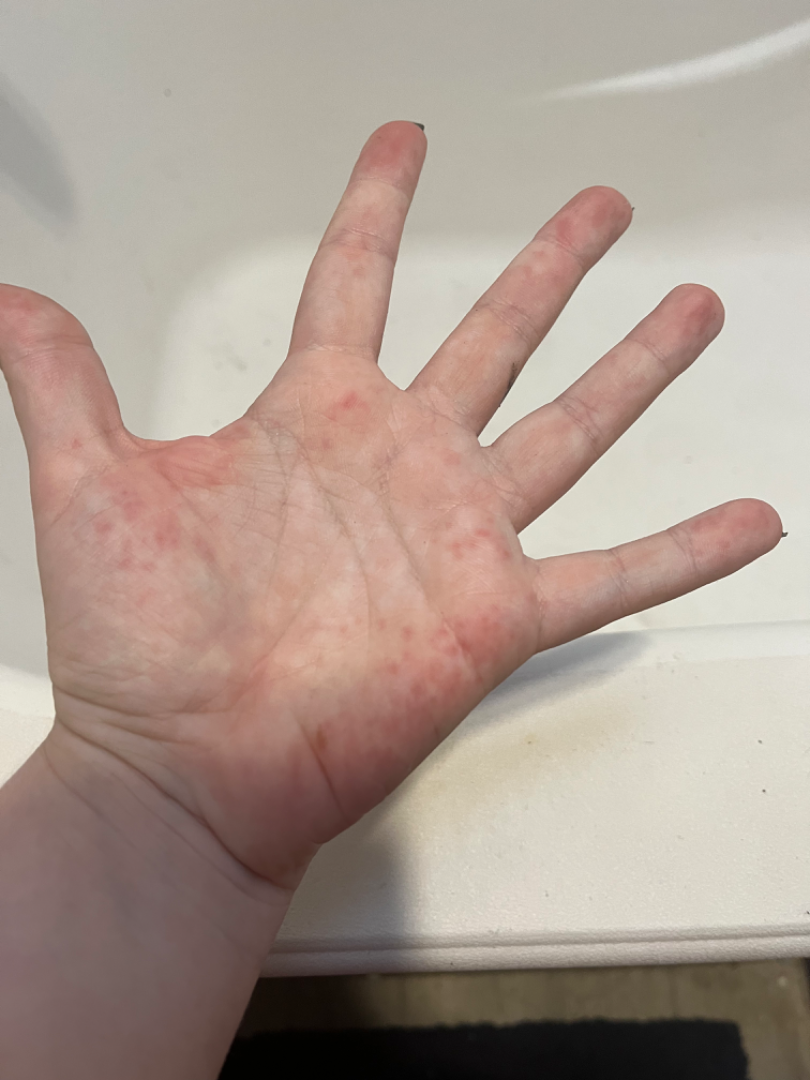The image was not sufficient for the reviewer to characterize the skin condition. Located on the palm and top or side of the foot. This image was taken at a distance. Female contributor, age 18–29.